A dermoscopic image of a skin lesion: 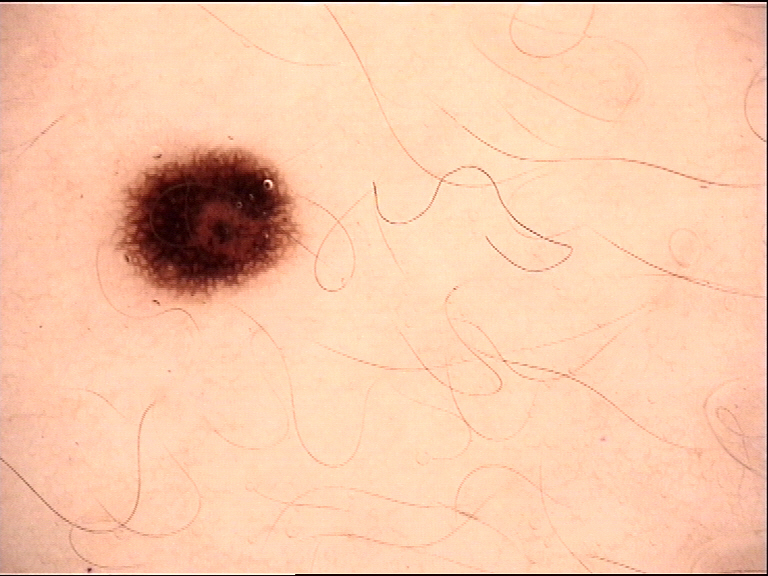assessment: dysplastic junctional nevus (expert consensus).